A dermoscopy image of a skin lesion. A moderate number of moles by the patient's own estimate. A female subject 50 years of age. The patient says their skin reddens painfully with sun exposure — 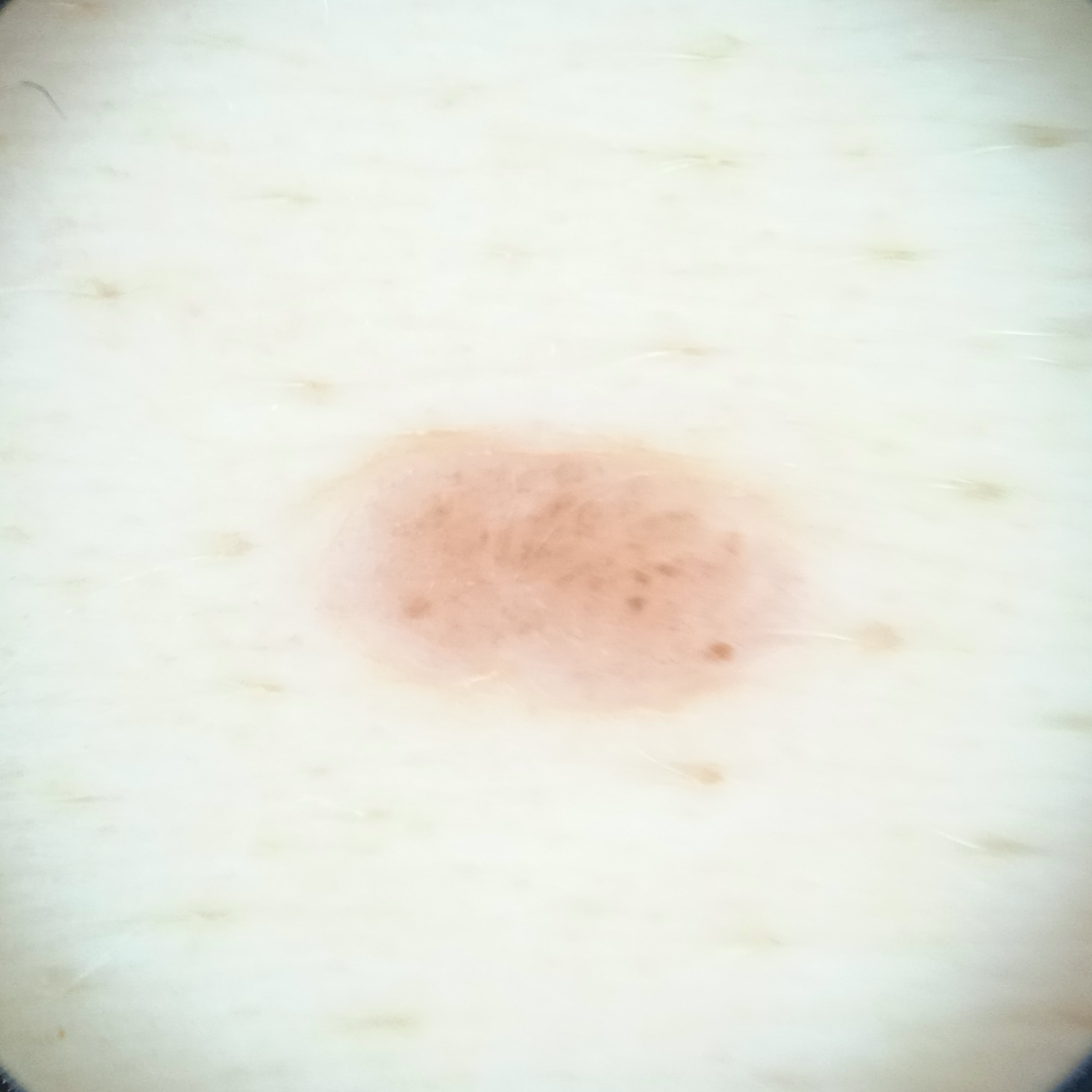Q: What was the diagnosis?
A: melanocytic nevus (dermatologist consensus)